A dermatoscopic image of a skin lesion: 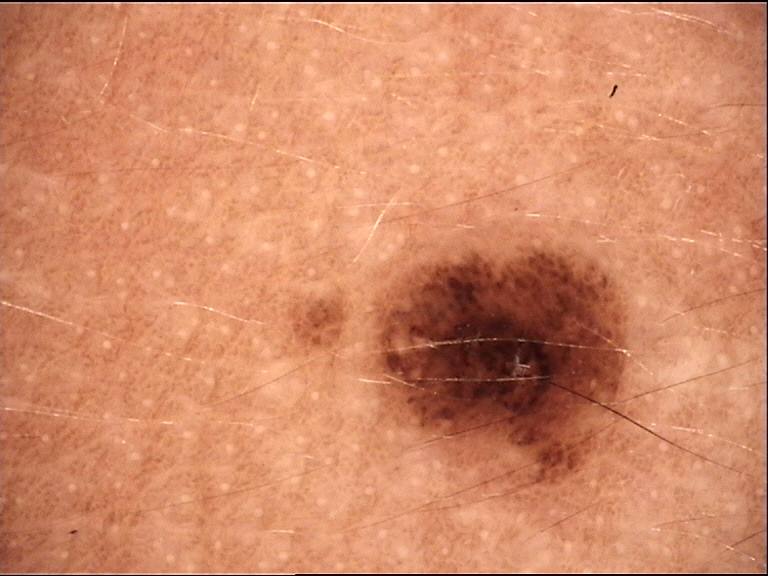| feature | finding |
|---|---|
| label | dysplastic junctional nevus (expert consensus) |